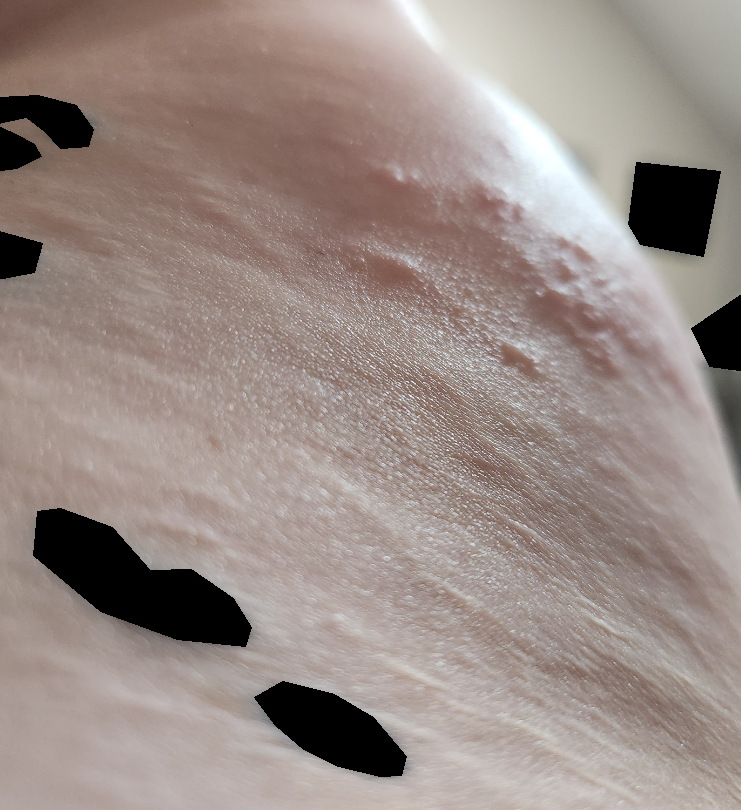Findings:
– diagnostic considerations — favoring Urticaria; also on the differential is Eczema; an alternative is Allergic Contact Dermatitis; less probable is Pruritic urticarial papules and plaques of pregnancy; less likely is Scabies